The chart documents a prior melanoma · a female subject in their 40s · a dermoscopic close-up of a skin lesion · the patient is Fitzpatrick skin type I — 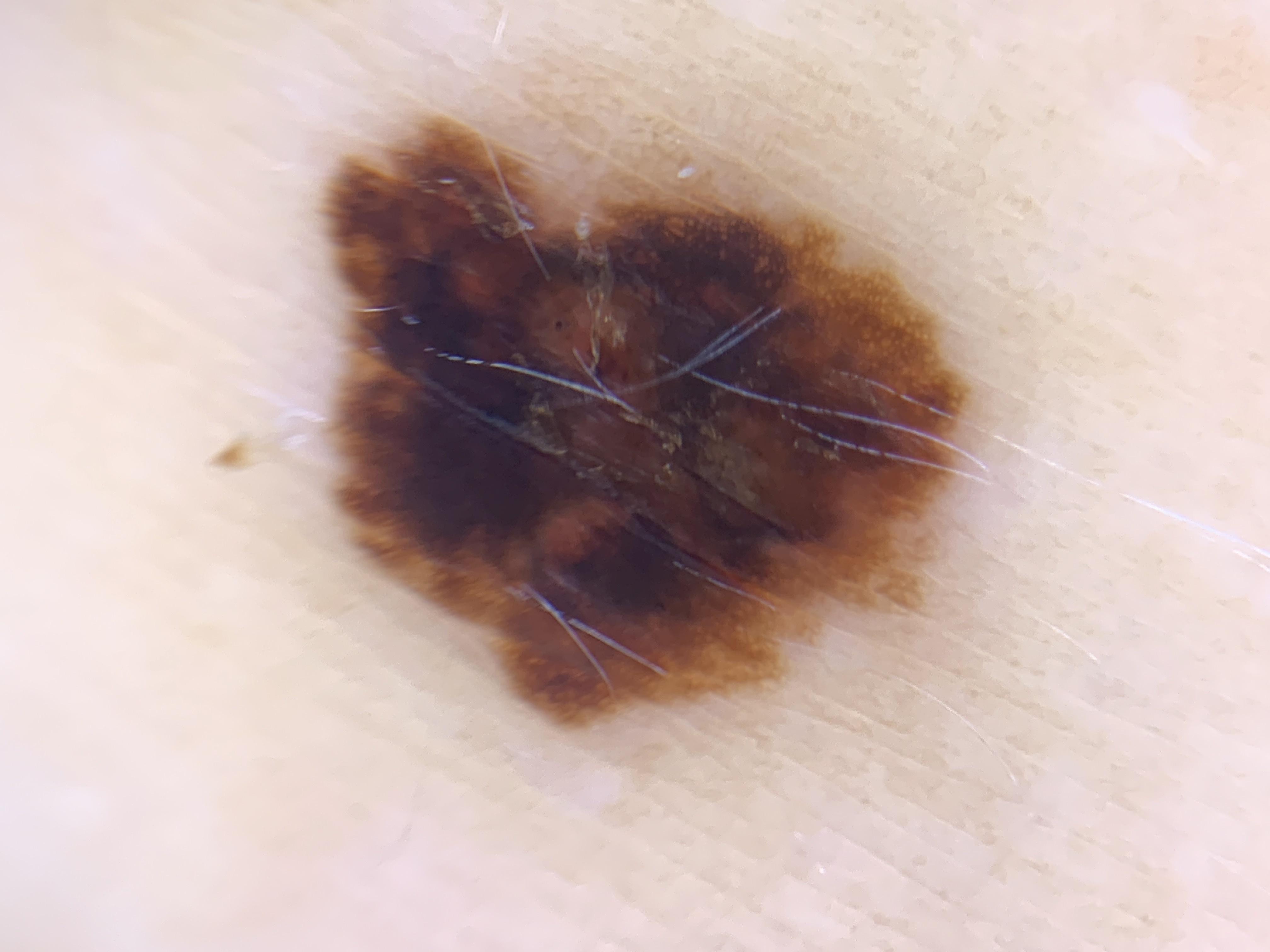– location: the trunk (the posterior trunk)
– diagnosis: Melanoma (biopsy-proven)